The lesion involves the arm and leg; this image was taken at an angle; no constitutional symptoms were reported; the condition has been present for more than one year; the patient is female; symptoms reported: darkening and enlargement:
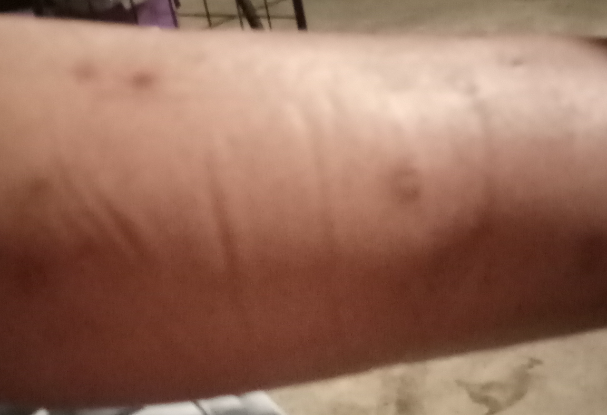Findings:
No differential diagnosis could be assigned on photographic review.